The lesion involves the arm · a close-up photograph · the subject is a female aged 50–59.
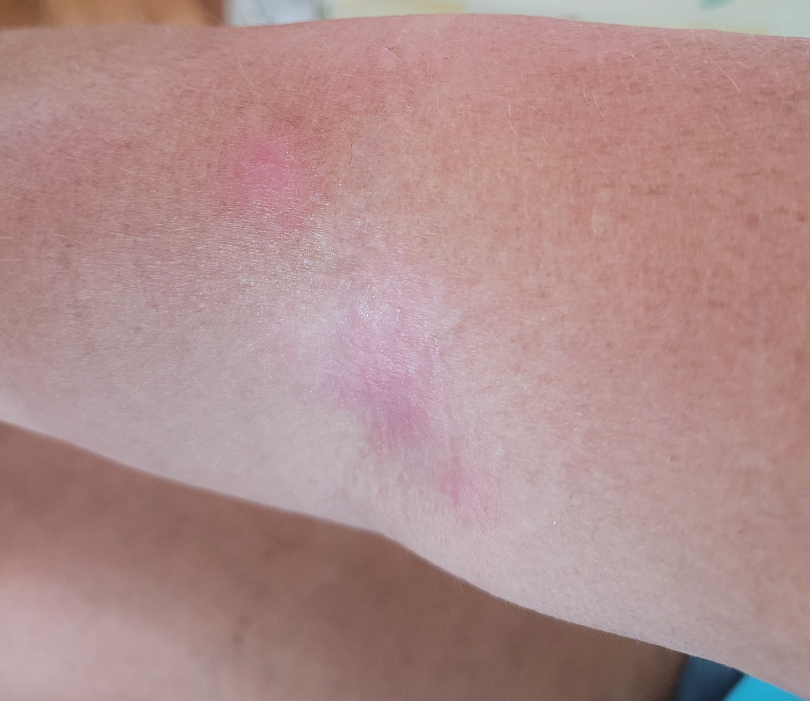Texture is reported as flat. Self-categorized by the patient as a rash. The lesion is associated with bothersome appearance, itching, burning and enlargement. No associated systemic symptoms reported. The patient reports the condition has been present for three to twelve months. The reviewing clinician's impression was: in keeping with Eczema.